This is a close-up image, the arm is involved:
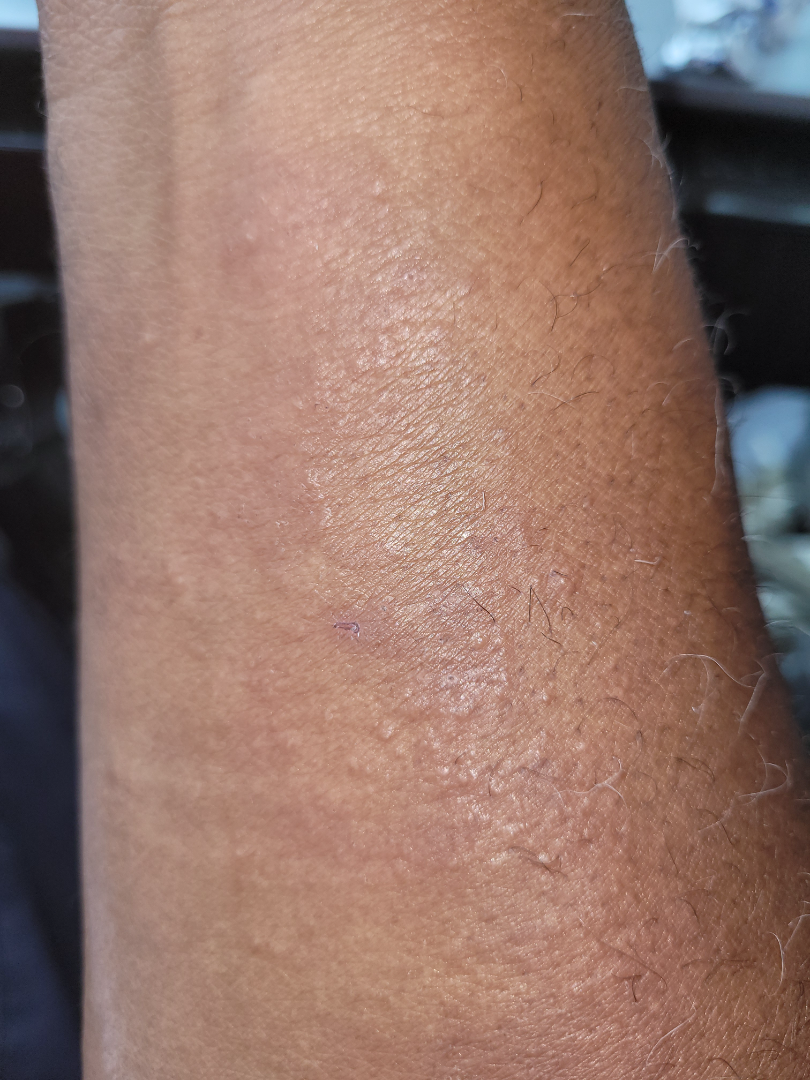Skin tone: Fitzpatrick V.
The lesion is described as raised or bumpy.
A single dermatologist reviewed the case: most consistent with Acute dermatitis, NOS.